The photo was captured at an angle. The arm and head or neck are involved. Male patient, age 18–29.
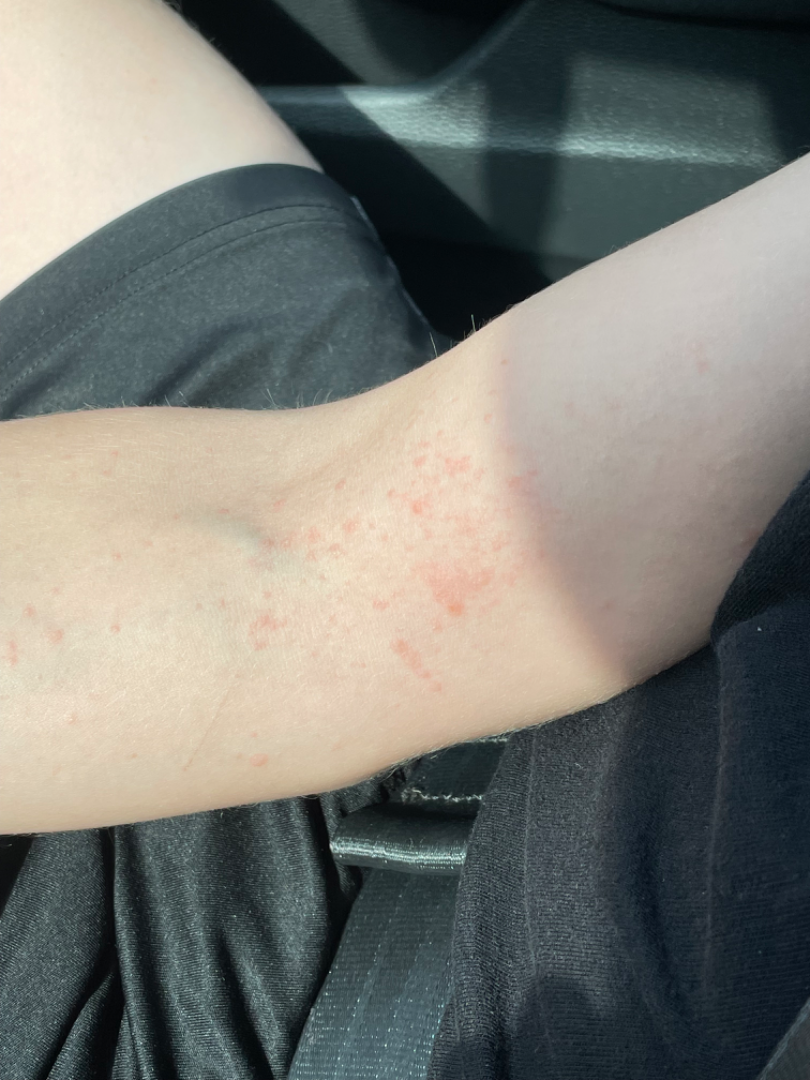On dermatologist assessment of the image, Eczema and Acute dermatitis, NOS were each considered, in no particular order.